Reported duration is about one day · the patient described the issue as a pigmentary problem · the lesion involves the front of the torso and back of the torso · skin tone: non-clinician graders estimated Monk Skin Tone 8 (US pool) or 4 (India pool) · the photograph is a close-up of the affected area · texture is reported as raised or bumpy.
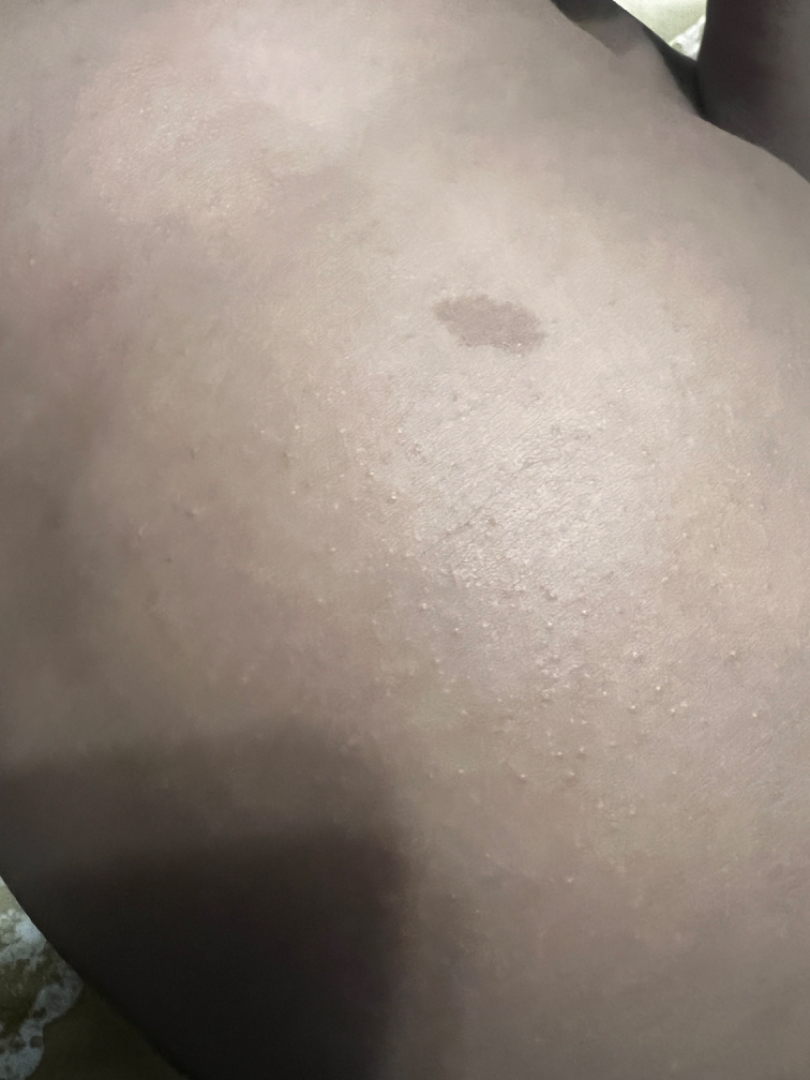  assessment: indeterminate from the photograph